Dermoscopy of a skin lesion: 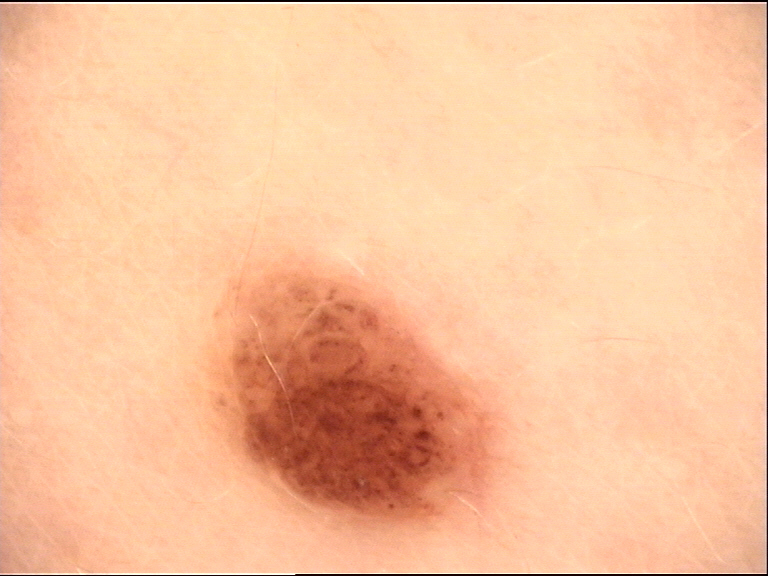Findings:
The architecture is that of a banal lesion.
Impression:
Labeled as a compound nevus.